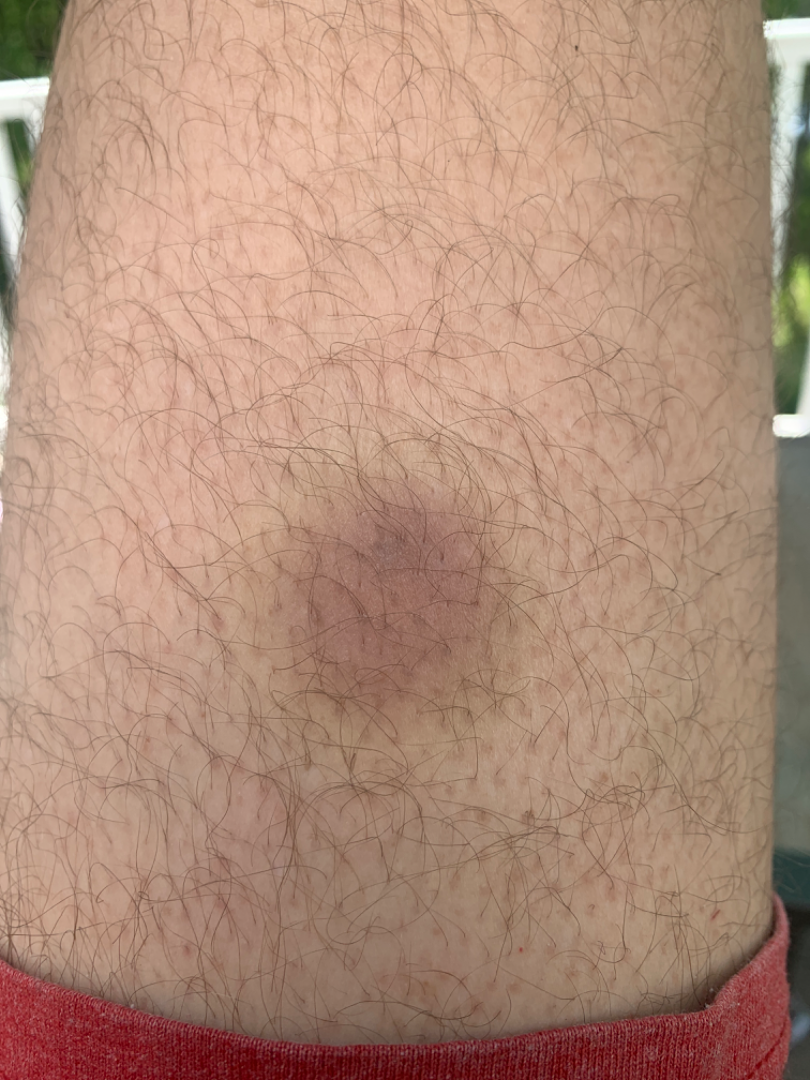The lesion is described as flat.
This is a close-up image.
The patient described the issue as a pigmentary problem.
Reported lesion symptoms include darkening and bothersome appearance.
Located on the leg.
The contributor is 40–49, male.
The primary impression is Drug Rash; also raised was ecchymoses.